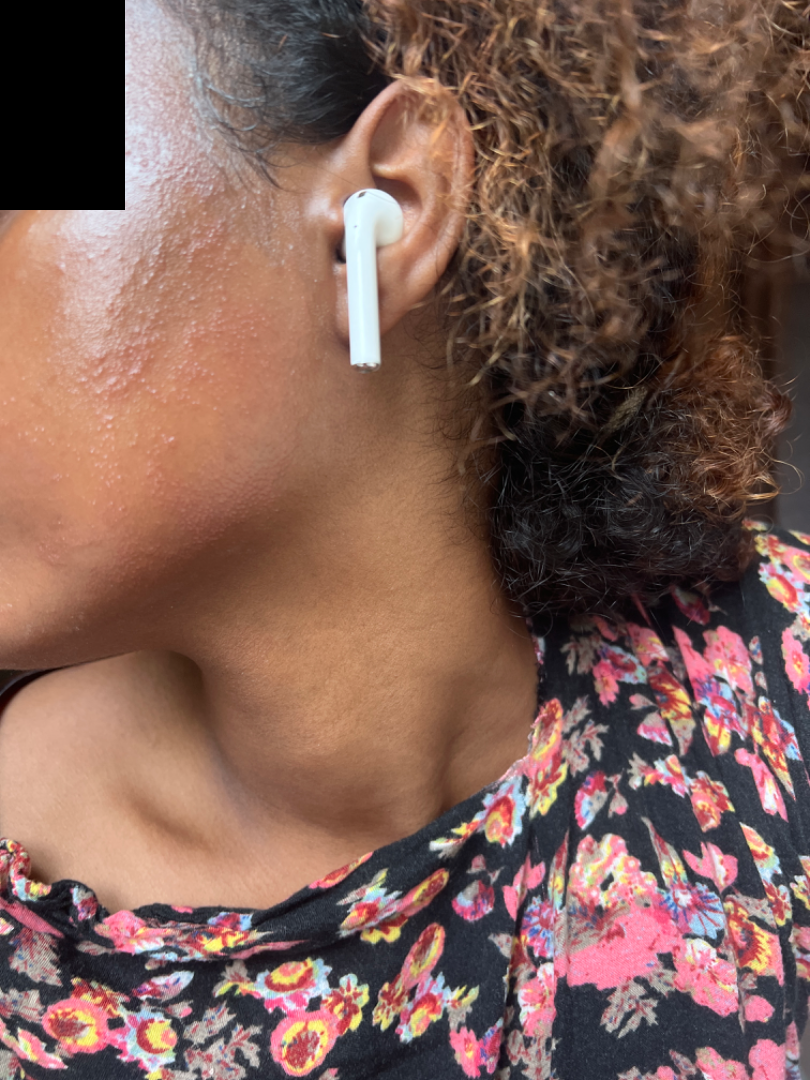Notes:
– diagnostic considerations — Contact dermatitis (possible); Allergic Contact Dermatitis (possible); Acne (remote); Miliaria (remote)